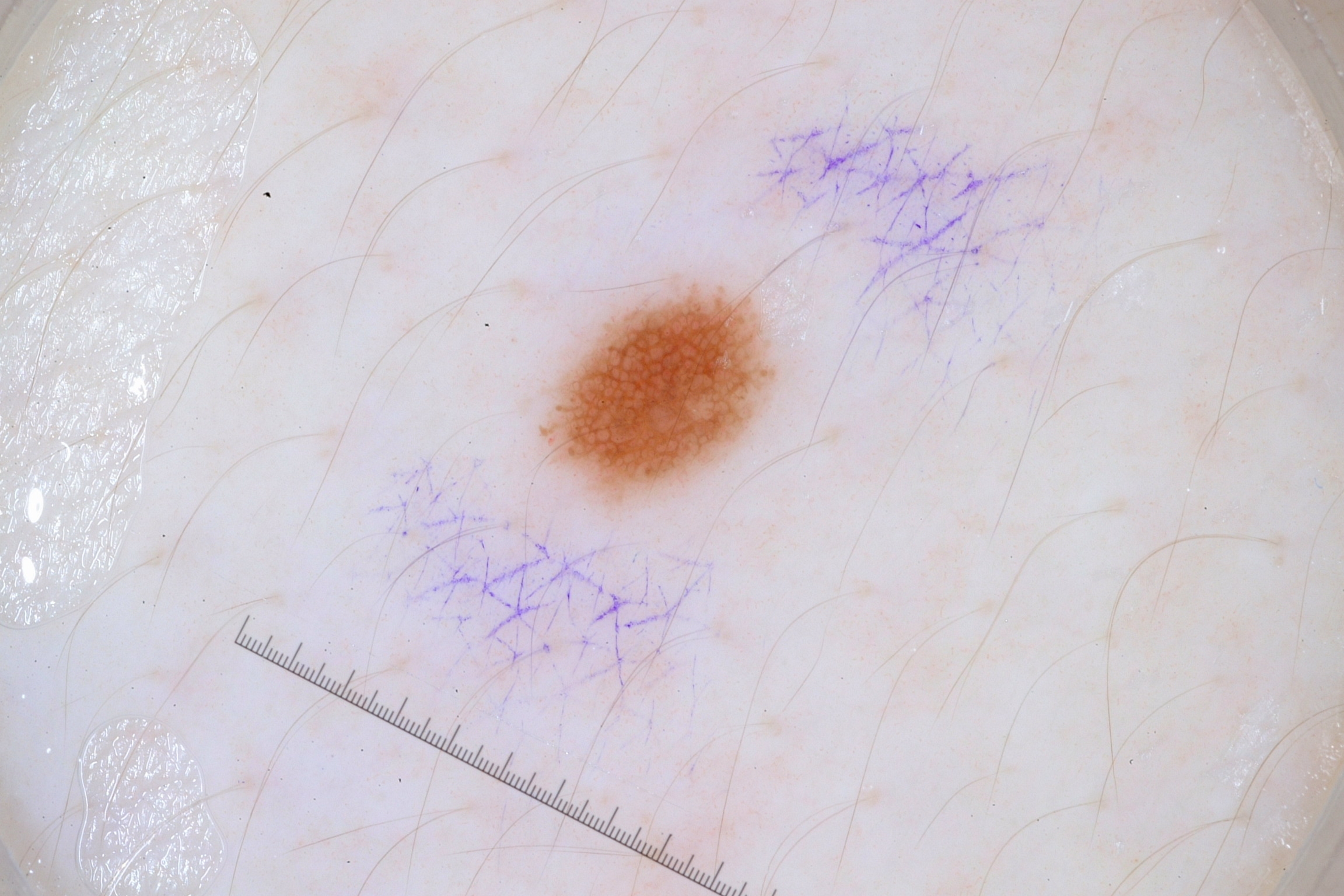This is a dermoscopic photograph of a skin lesion. A female patient aged around 30. The lesion occupies the region left=540, top=285, right=775, bottom=499. Dermoscopic examination shows pigment network, with no milia-like cysts, negative network, or streaks. Diagnosed as a melanocytic nevus.